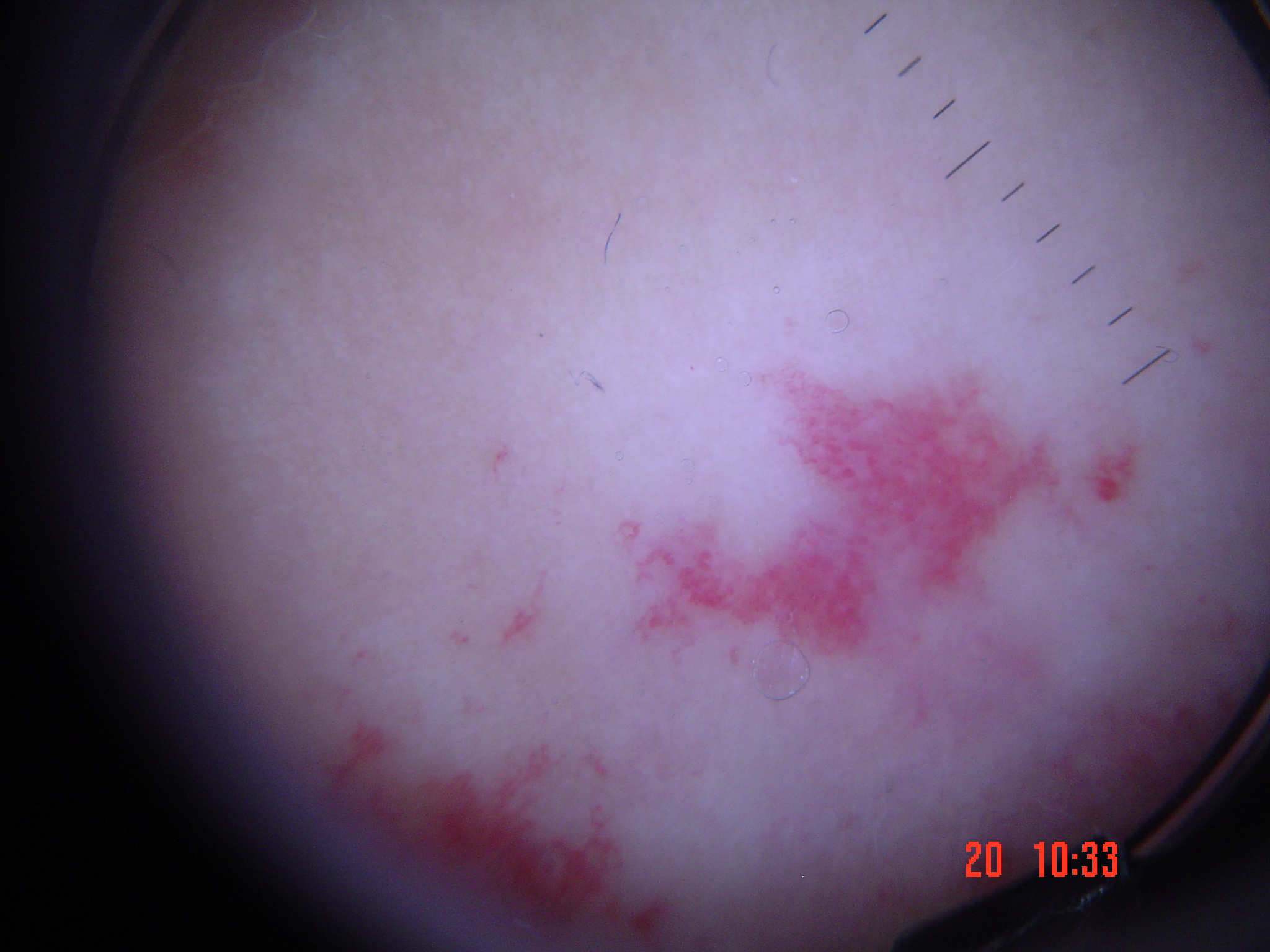| key | value |
|---|---|
| class | hemangioma (expert consensus) |